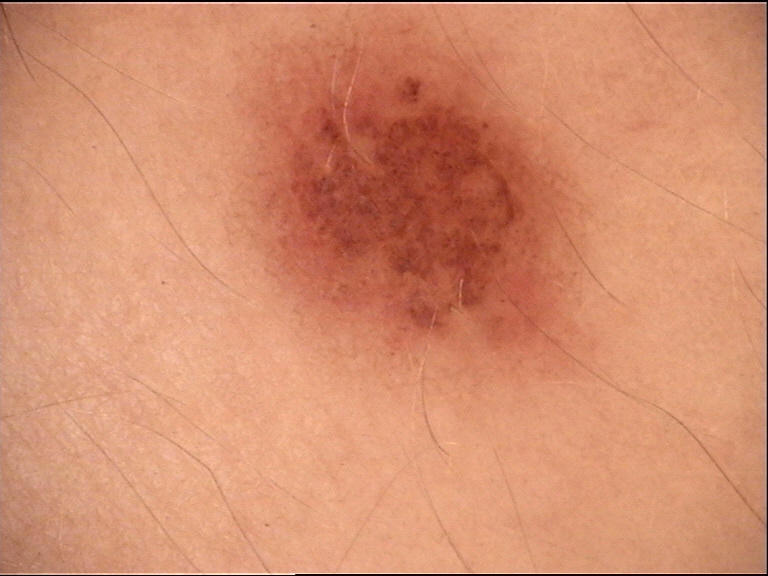The diagnosis was a compound nevus.